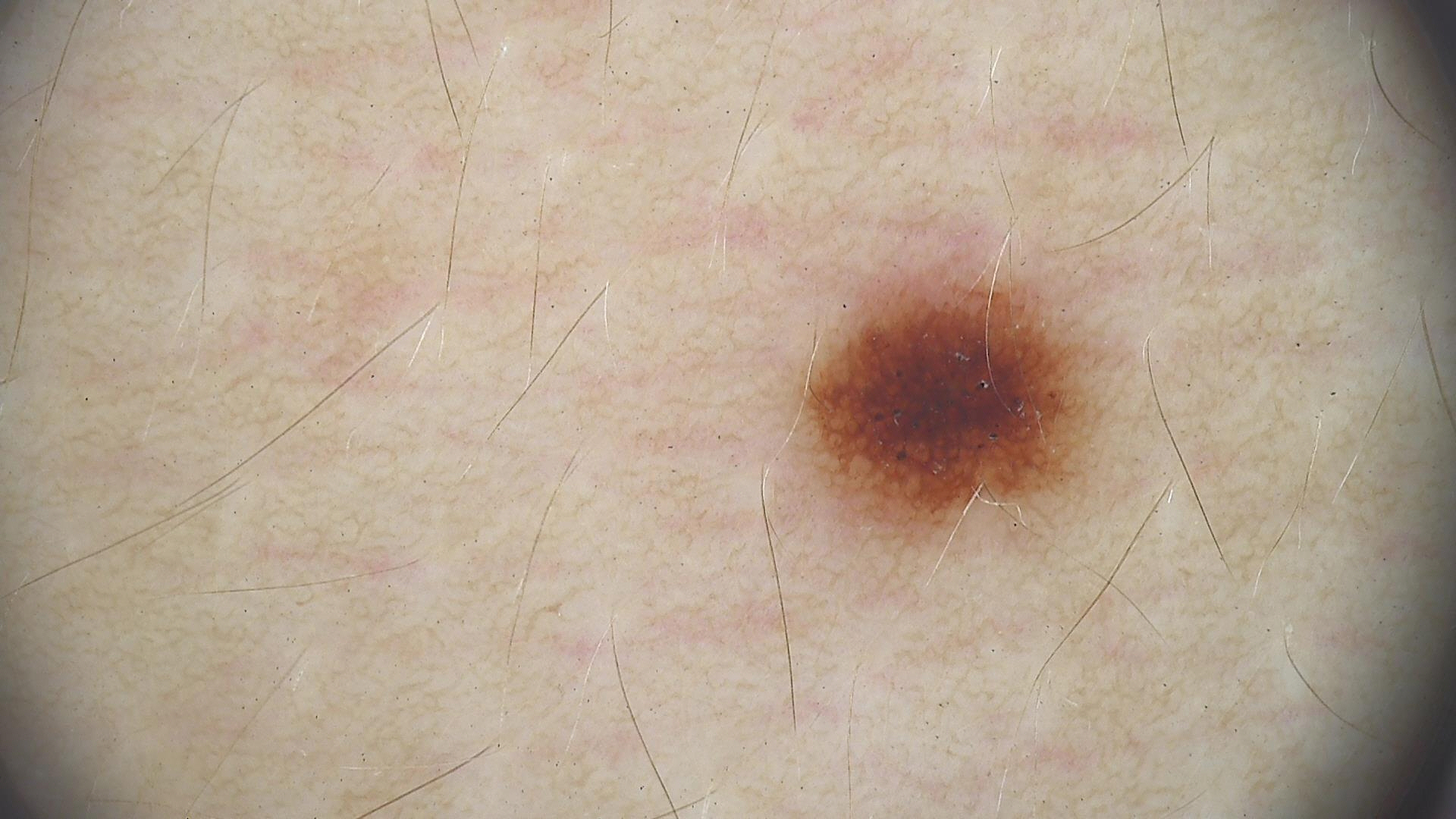diagnosis: dysplastic junctional nevus (expert consensus).